A dermatoscopic image of a skin lesion:
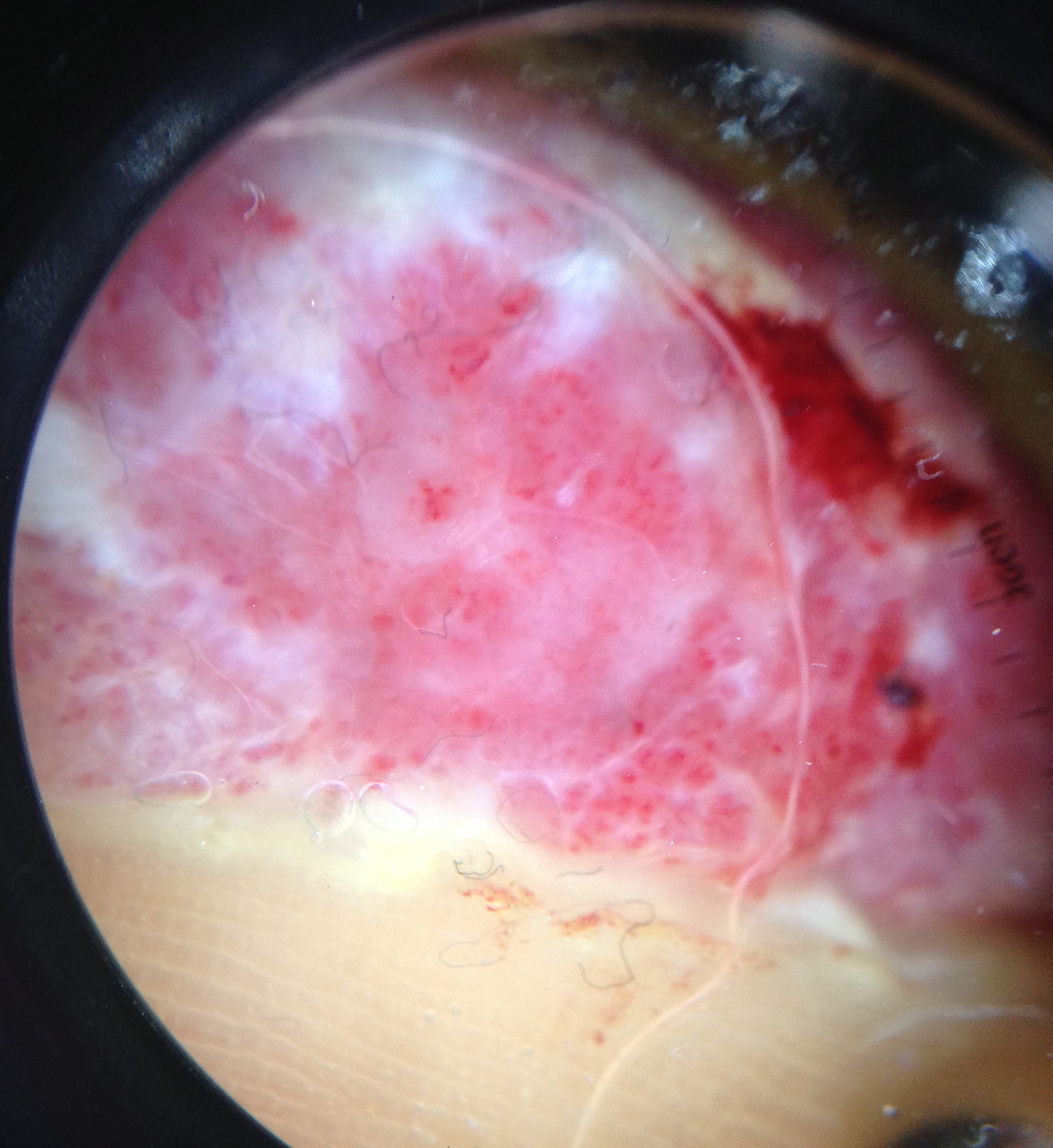Histopathologically confirmed as a malignant lesion — an acral nodular melanoma.